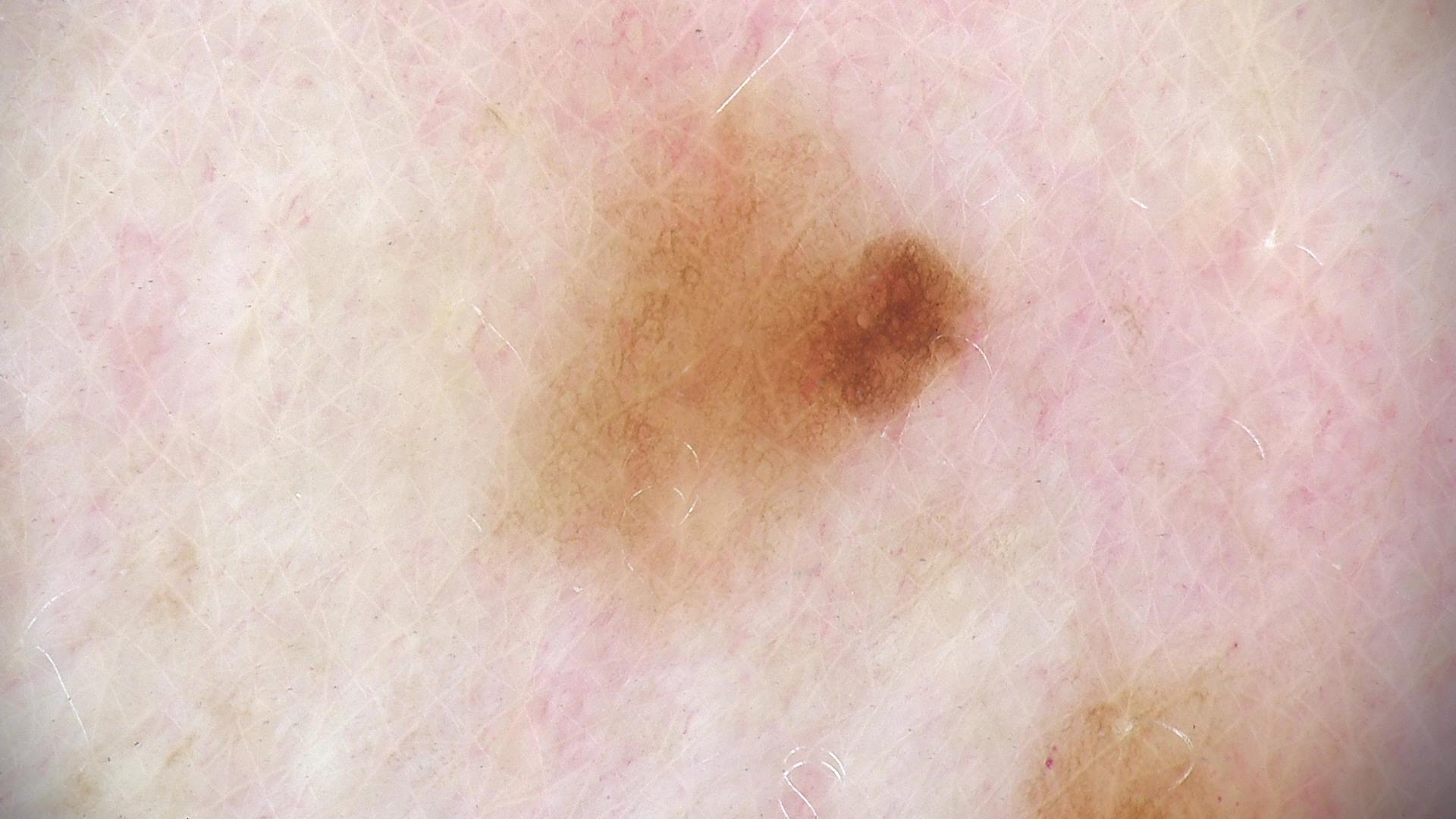Labeled as a benign lesion — a dysplastic junctional nevus.